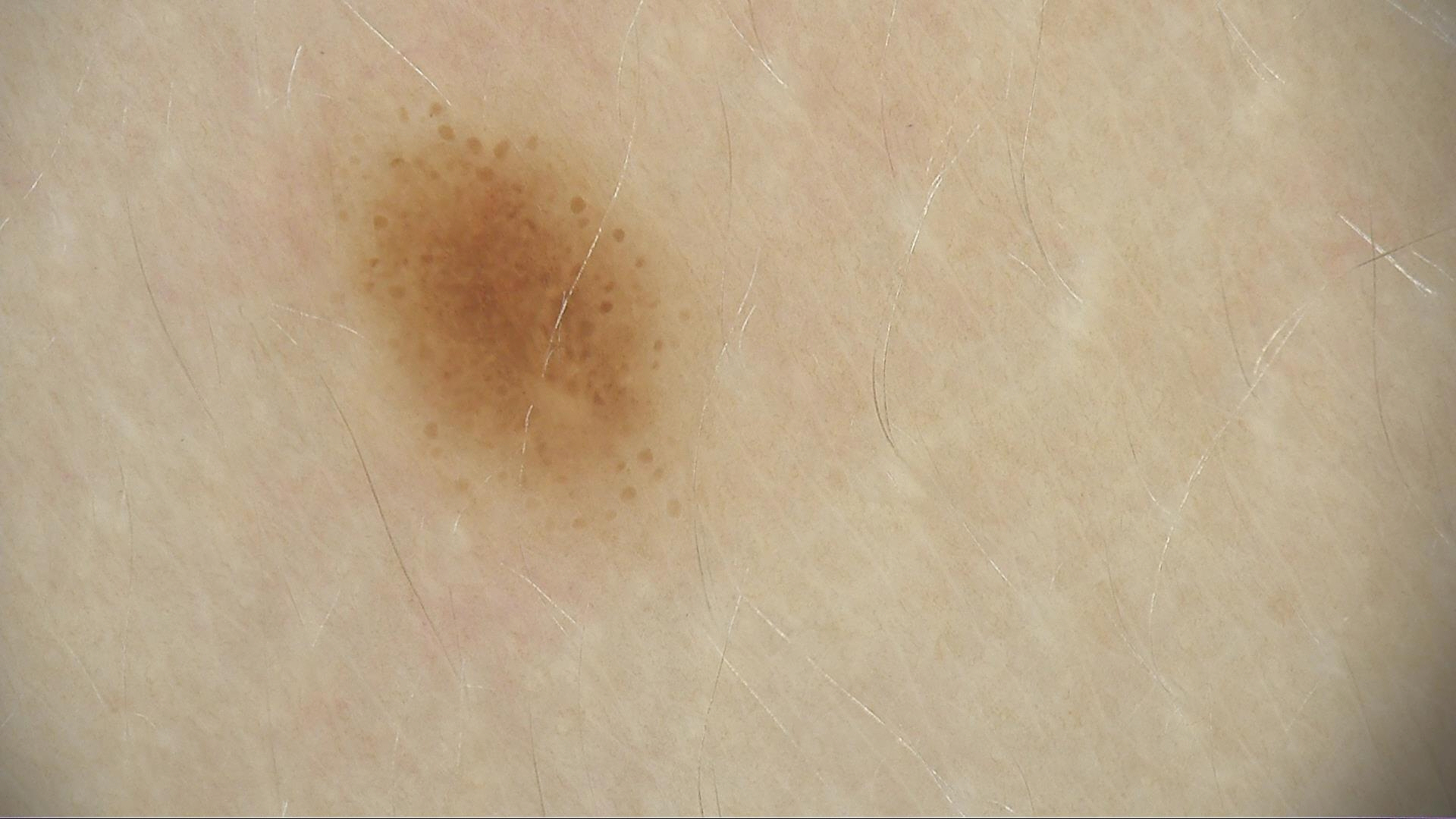Case: A dermoscopic close-up of a skin lesion. Impression: Diagnosed as a dysplastic junctional nevus.